The chart records pesticide exposure, prior skin cancer (patient or family), and alcohol use; recorded as FST II; a clinical photo of a skin lesion taken with a smartphone: 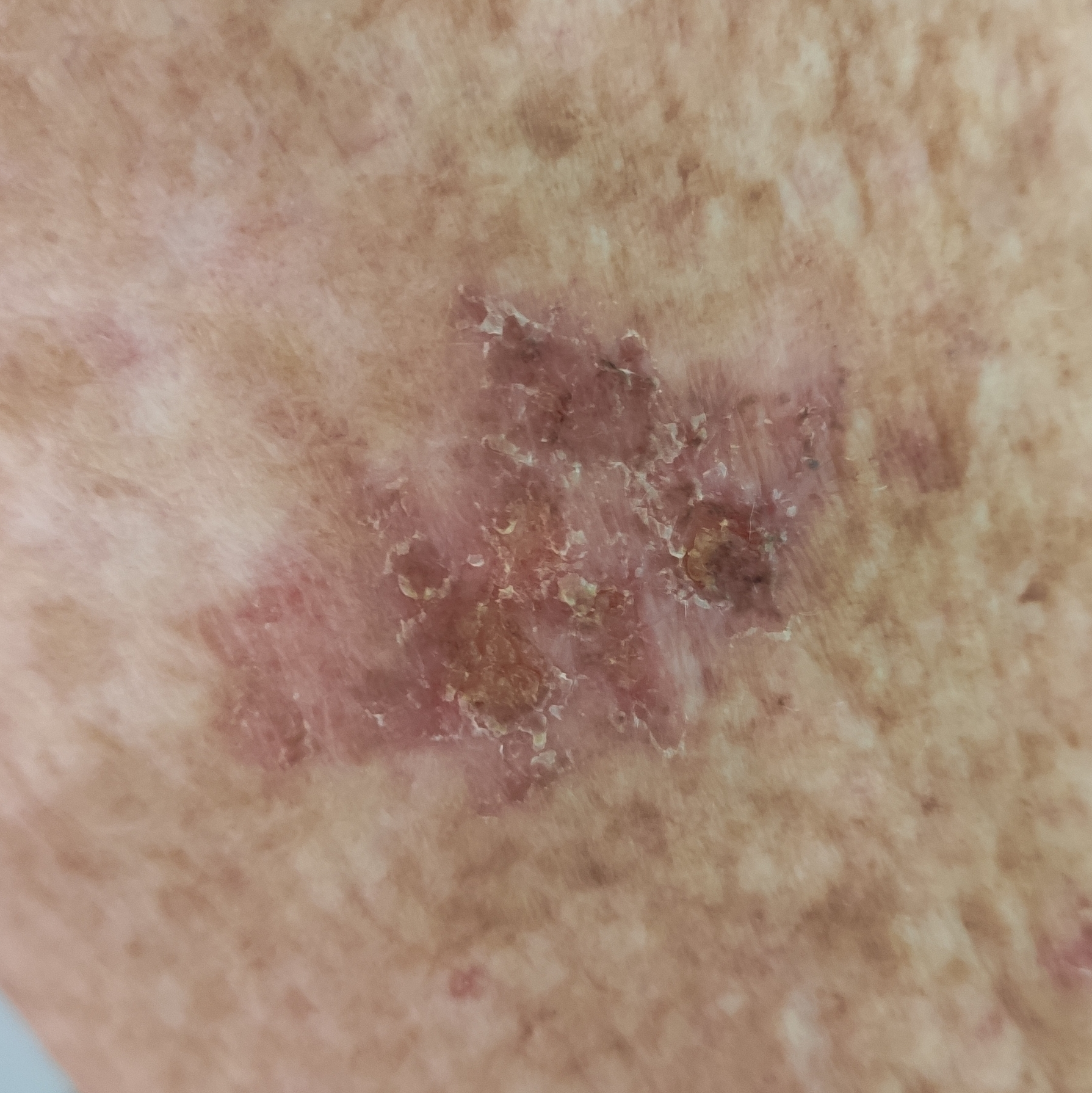{
  "lesion_location": "an arm",
  "lesion_size": {
    "diameter_1_mm": 30.0,
    "diameter_2_mm": 20.0
  },
  "symptoms": {
    "present": [
      "bleeding",
      "pain",
      "elevation",
      "itching",
      "growth"
    ]
  },
  "diagnosis": {
    "name": "basal cell carcinoma",
    "code": "BCC",
    "malignancy": "malignant",
    "confirmation": "histopathology"
  }
}